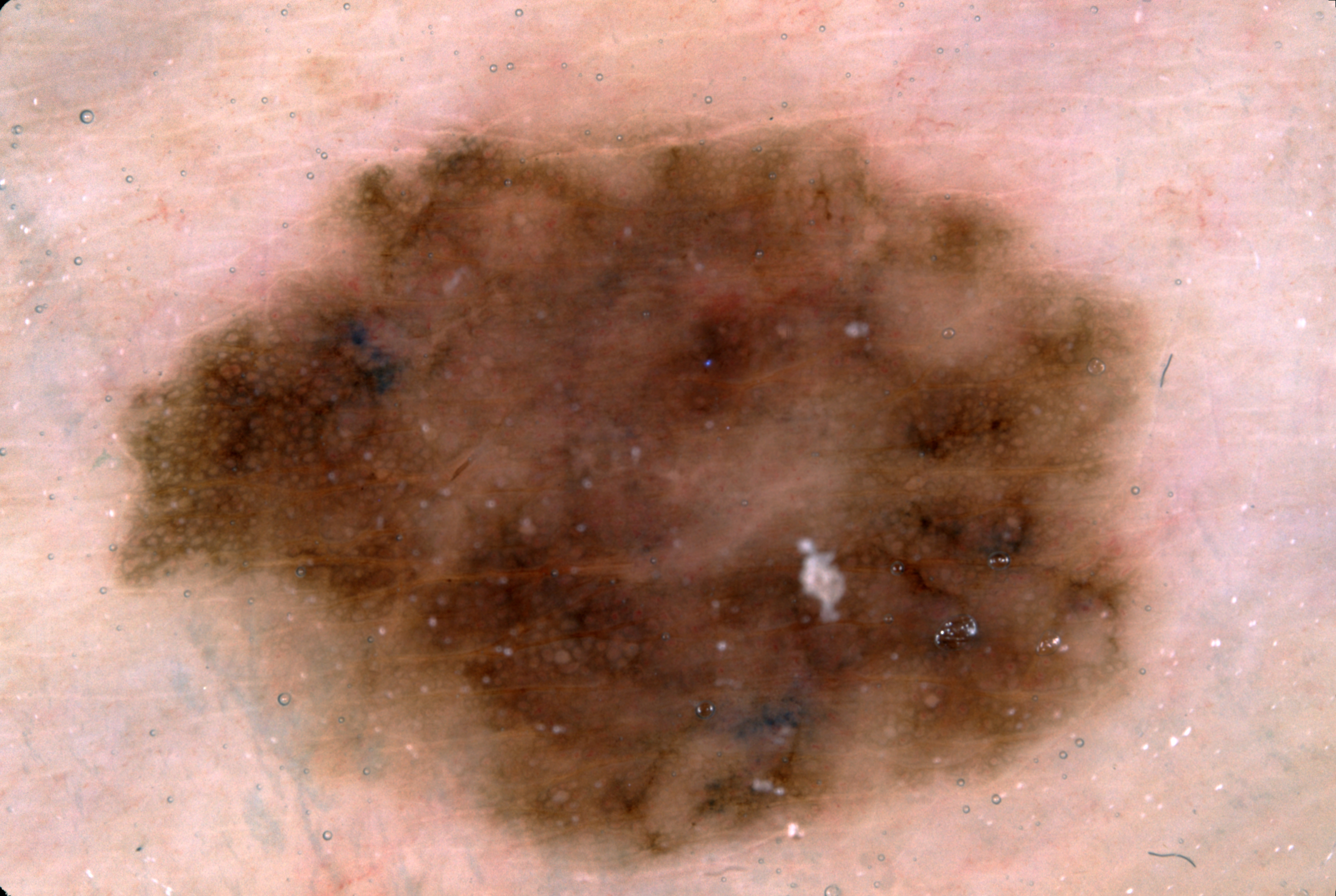  image:
    modality: dermoscopy
  patient:
    sex: female
    age_approx: 65
  dermoscopic_features:
    present:
      - pigment network
      - negative network
    absent:
      - streaks
      - milia-like cysts
  lesion_location:
    bbox_xyxy:
      - 115
      - 112
      - 1158
      - 868
  diagnosis:
    name: melanocytic nevus
    malignancy: benign
    lineage: melanocytic
    provenance: clinical